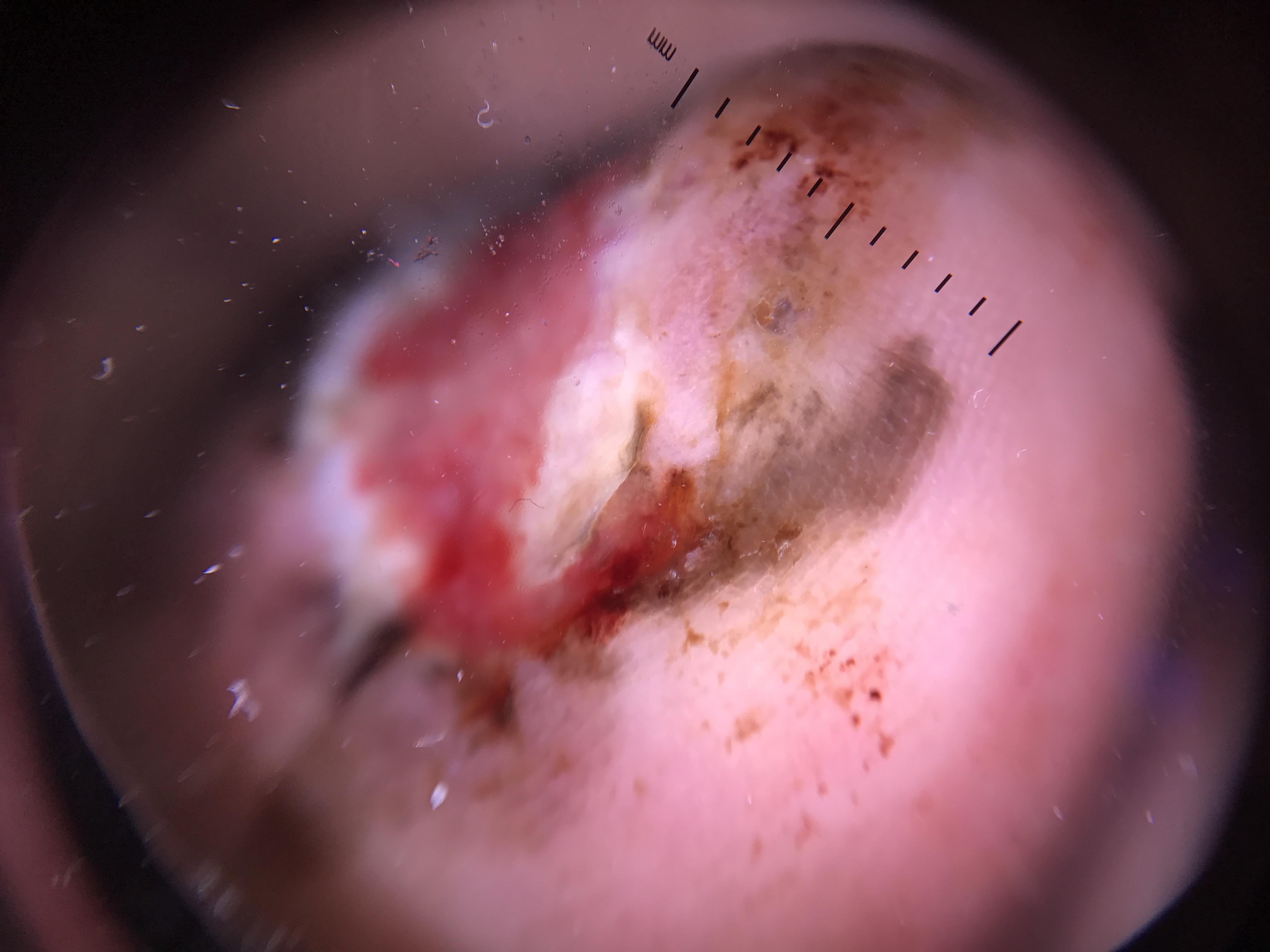Recorded as Fitzpatrick III. The chart records a previous melanoma. The lesion is located on a lower extremity. Histopathological examination showed a melanoma.